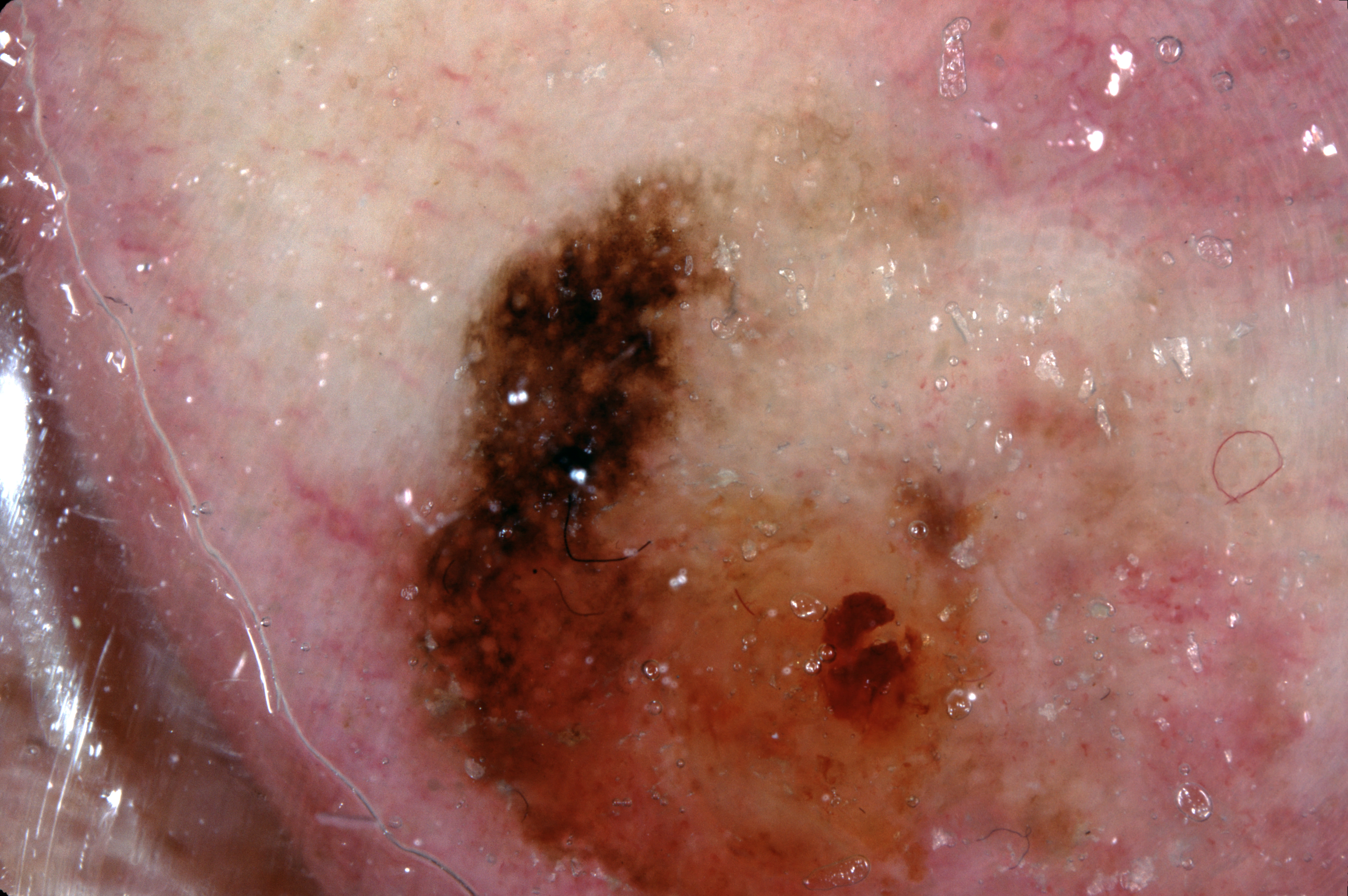{
  "image": {
    "modality": "dermoscopy"
  },
  "patient": {
    "sex": "male",
    "age_approx": 75
  },
  "dermoscopic_features": {
    "present": [],
    "absent": [
      "pigment network",
      "milia-like cysts",
      "negative network",
      "streaks"
    ]
  },
  "lesion_extent": "large",
  "lesion_location": {
    "bbox_xyxy": [
      389,
      104,
      1170,
      891
    ]
  },
  "diagnosis": {
    "name": "melanoma",
    "malignancy": "malignant",
    "lineage": "melanocytic",
    "provenance": "histopathology"
  }
}